A dermoscopic view of a skin lesion — 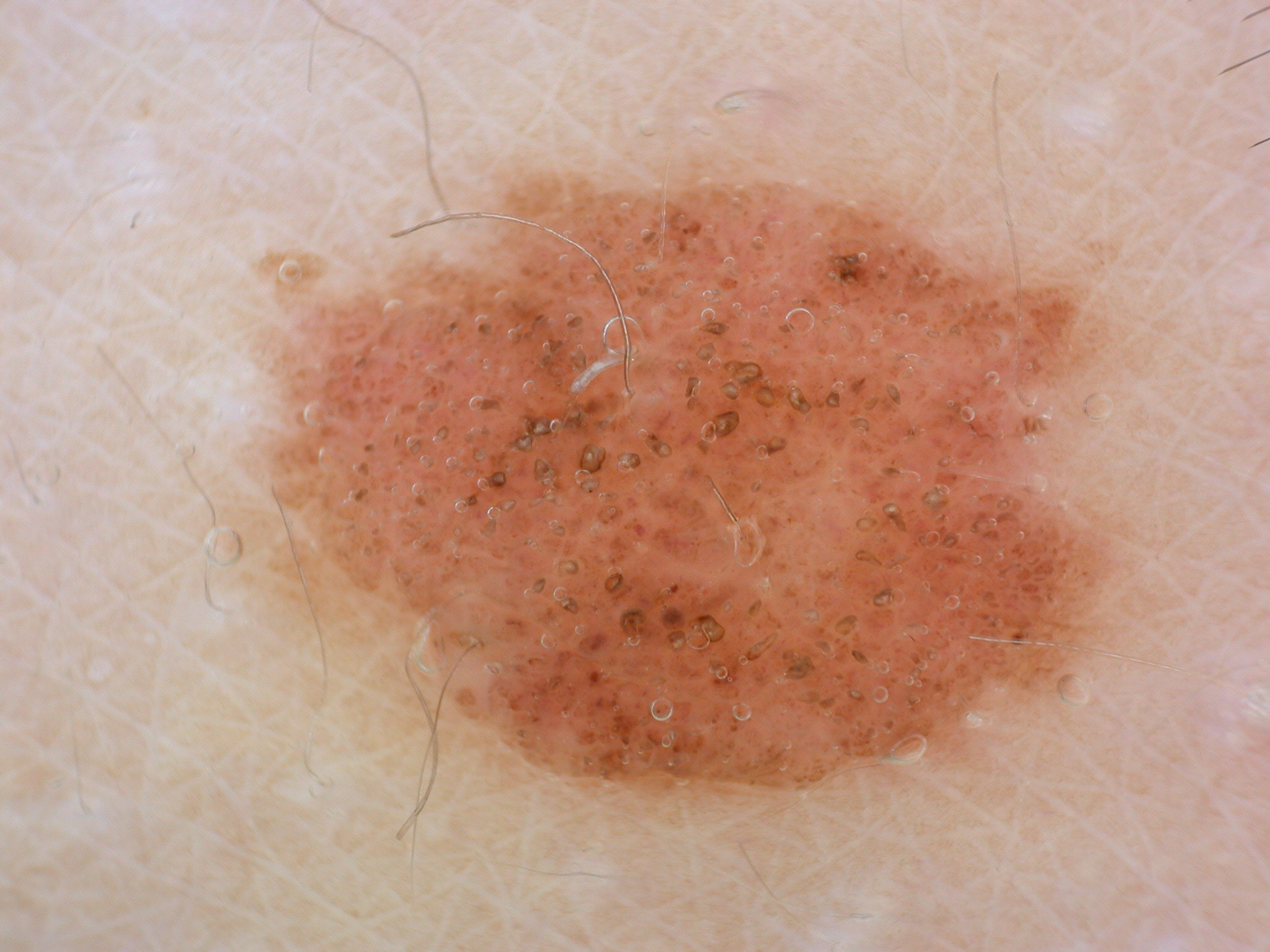Summary: Dermoscopy demonstrates no negative network, streaks, pigment network, milia-like cysts, or globules. With coordinates (x1, y1, x2, y2), the lesion is located at [235,153,1135,799]. Impression: Clinically diagnosed as a melanocytic nevus.